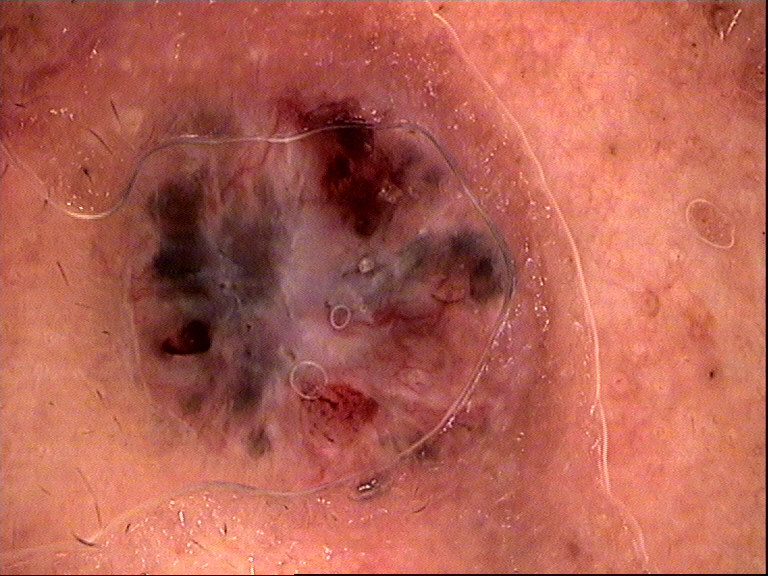image: dermatoscopy
lesion type: keratinocytic
pathology: basal cell carcinoma (biopsy-proven)